A clinical photo of a skin lesion taken with a smartphone · a male patient in their 60s:
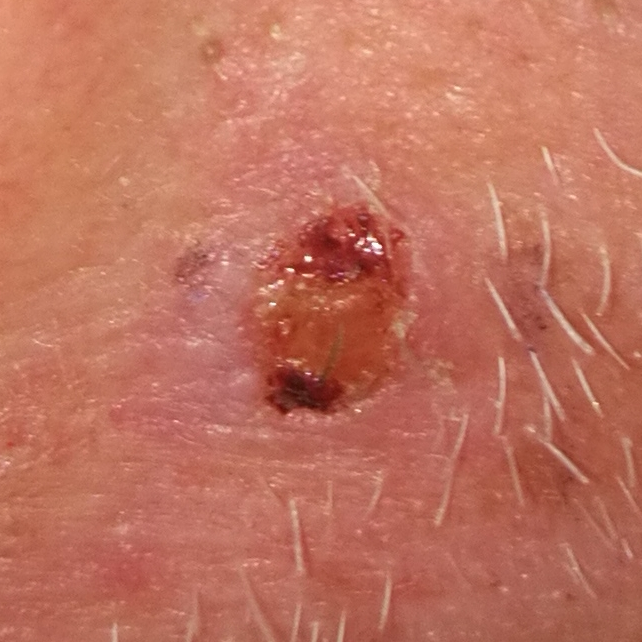{
  "lesion_location": "a lip",
  "symptoms": {
    "present": [
      "bleeding",
      "elevation",
      "pain",
      "itching",
      "growth"
    ]
  },
  "diagnosis": {
    "name": "basal cell carcinoma",
    "code": "BCC",
    "malignancy": "malignant",
    "confirmation": "histopathology"
  }
}